A female patient approximately 30 years of age. The patient was assessed as Fitzpatrick phototype III.
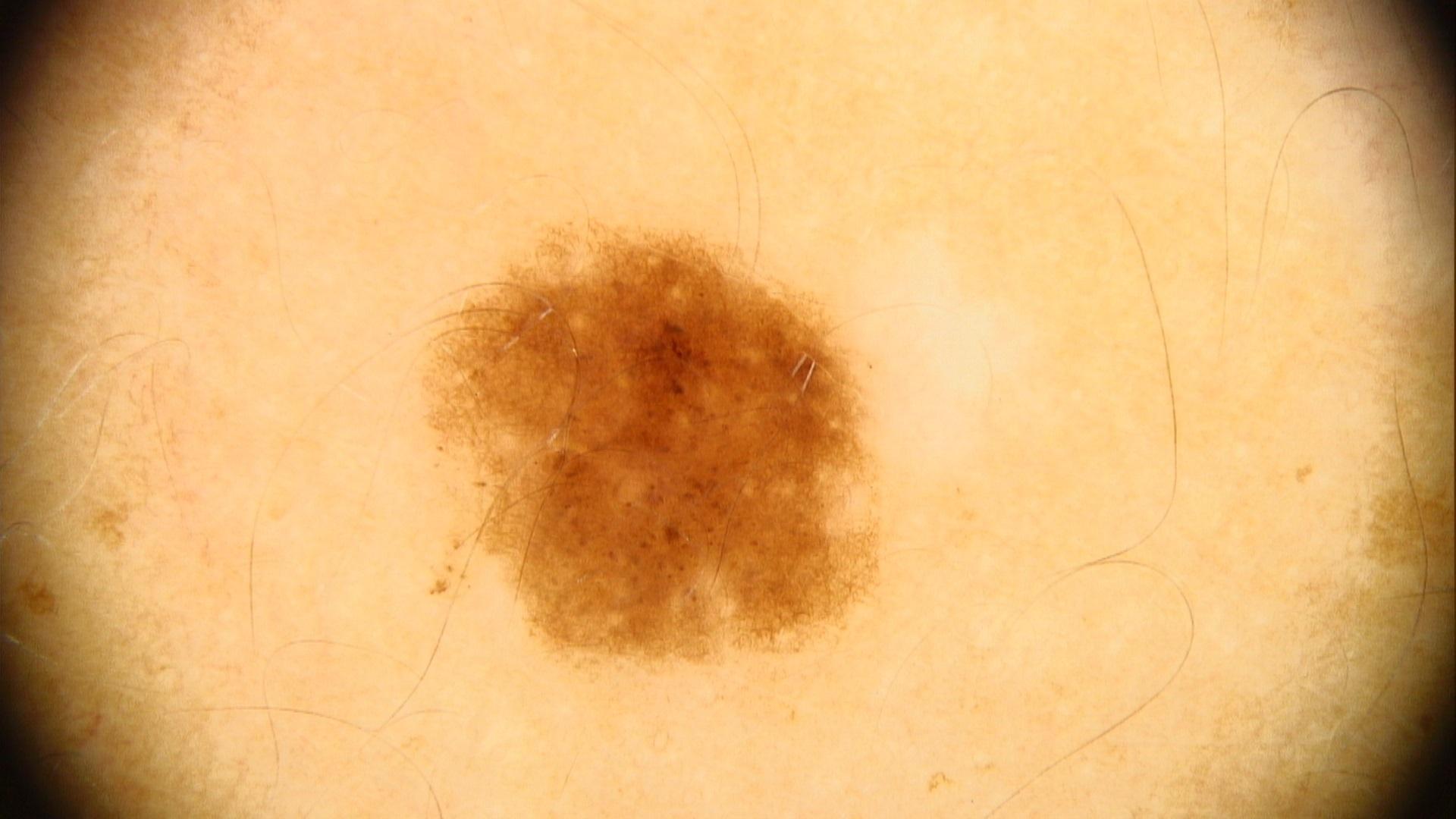Findings:
The lesion is on an upper extremity.
Impression:
Expert review favored a benign, melanocytic lesion — a nevus.